This is a close-up image. The patient is 30–39, male — 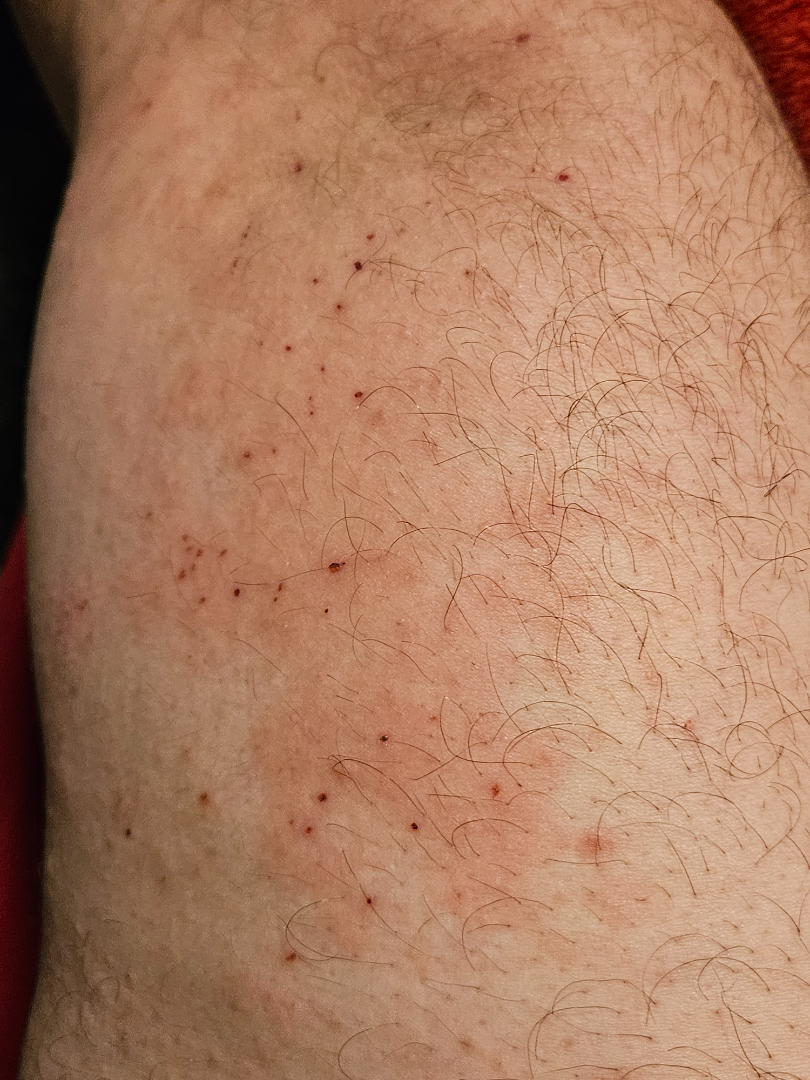On remote review of the image: Acute and chronic dermatitis (leading).